Located on the front of the torso; male subject, age 18–29; an image taken at a distance: 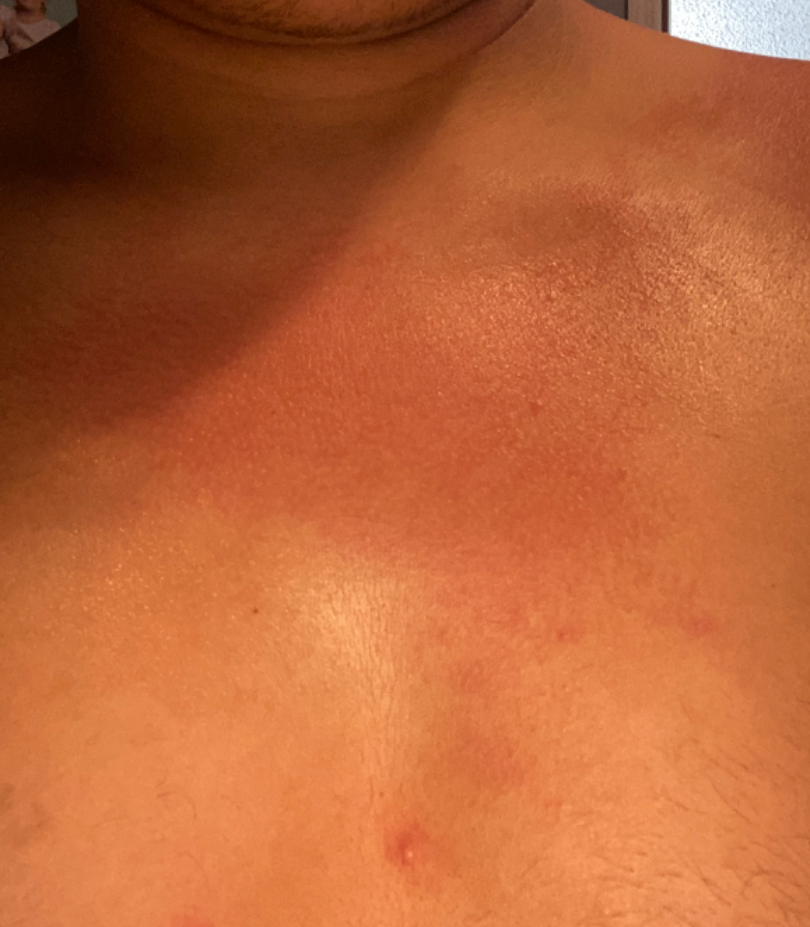Q: What was the assessment?
A: not assessable
Q: How does the patient describe it?
A: a rash
Q: How long has this been present?
A: about one day
Q: What symptoms does the patient report?
A: burning and itching
Q: What is the lesion texture?
A: flat